A dermoscopic image of a skin lesion; the subject is a male about 55 years old:
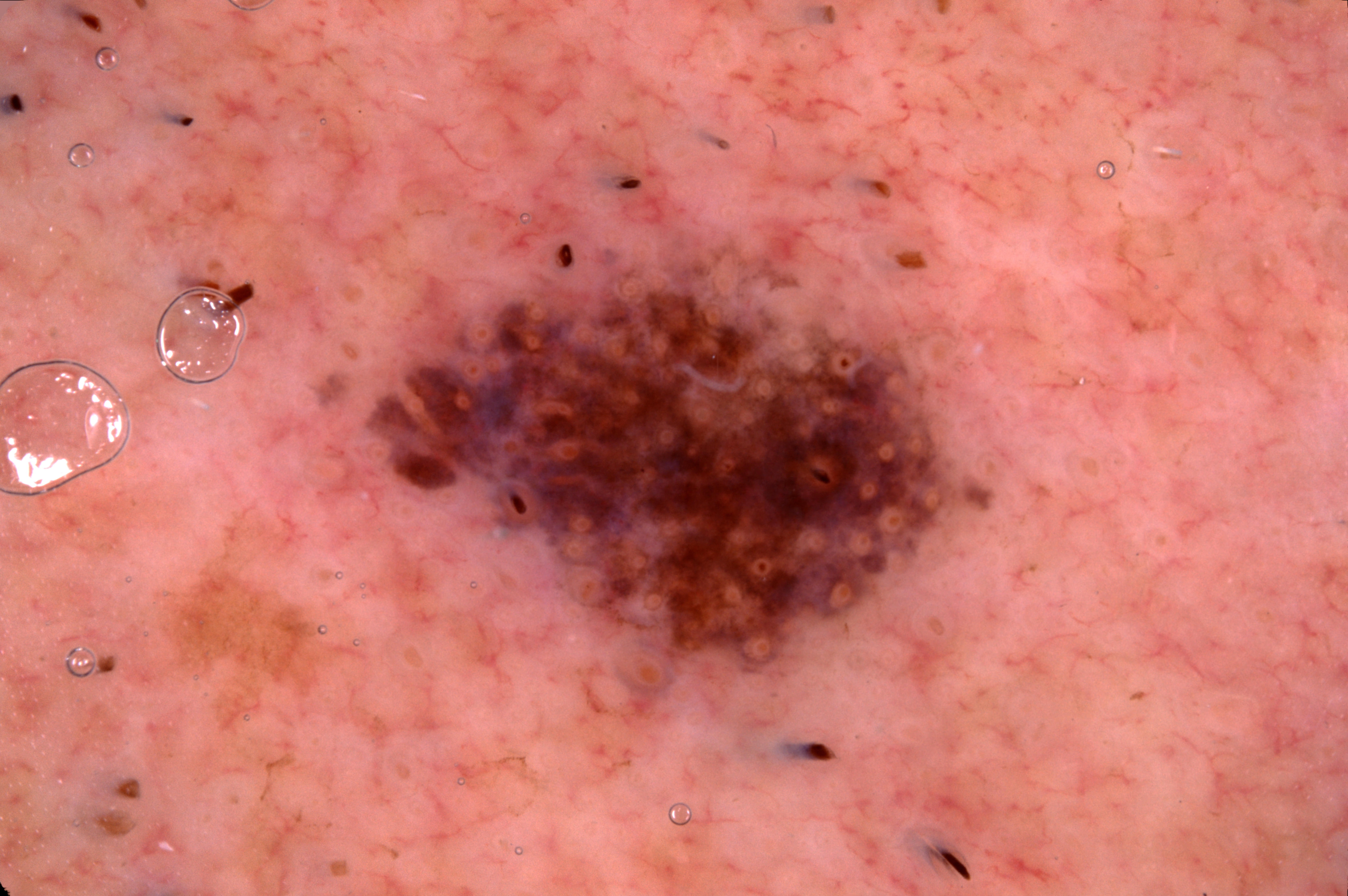Dermoscopic review identifies no milia-like cysts, streaks, pigment network, or negative network. The visible lesion spans <bbox>315, 212, 994, 687</bbox>. The diagnostic assessment was a melanocytic nevus.